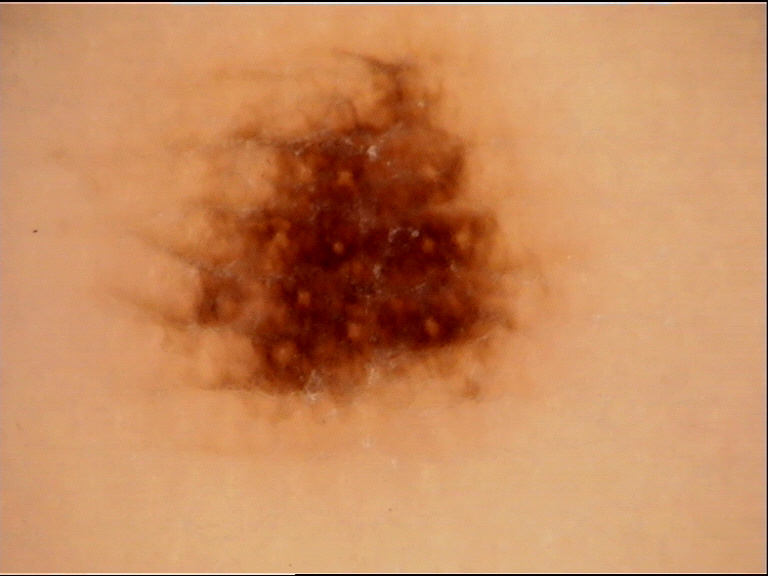lesion type: banal
label: acral junctional nevus (expert consensus)